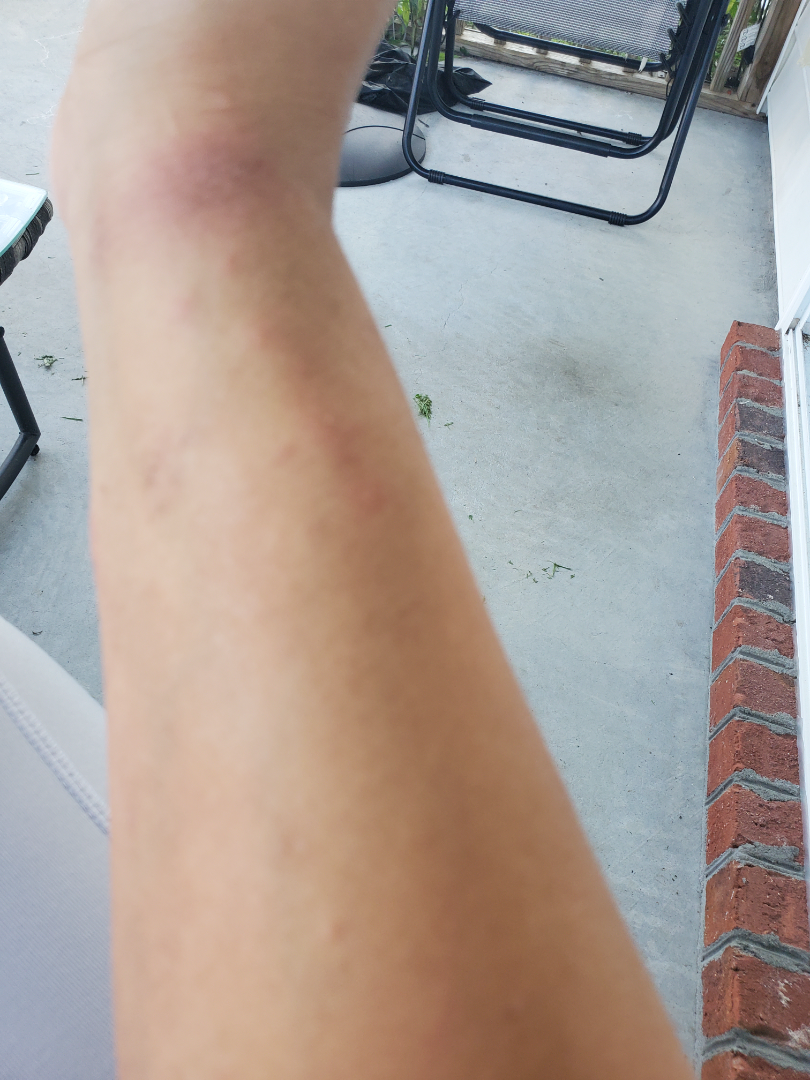Review:
The dermatologist could not determine a likely condition from the photograph alone.
Patient information:
Self-categorized by the patient as a rash. The contributor notes the condition has been present for one to four weeks. The contributor notes bothersome appearance, bleeding, itching and enlargement. No constitutional symptoms were reported. Close-up view. The leg and arm are involved. Female subject, age 40–49.